A smartphone photograph of a skin lesion; the chart notes prior skin cancer (patient or family) and pesticide exposure; the patient was assessed as Fitzpatrick II.
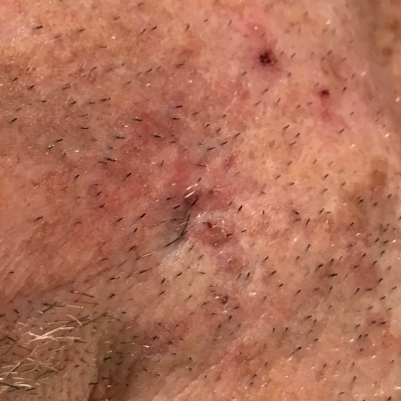Located on a foot.
Measuring about 5 × 4 mm.
By the patient's account, the lesion itches and is elevated.
Histopathology confirmed a malignancy — a squamous cell carcinoma.